Female subject, age 40–49. Located on the arm. This is a close-up image — 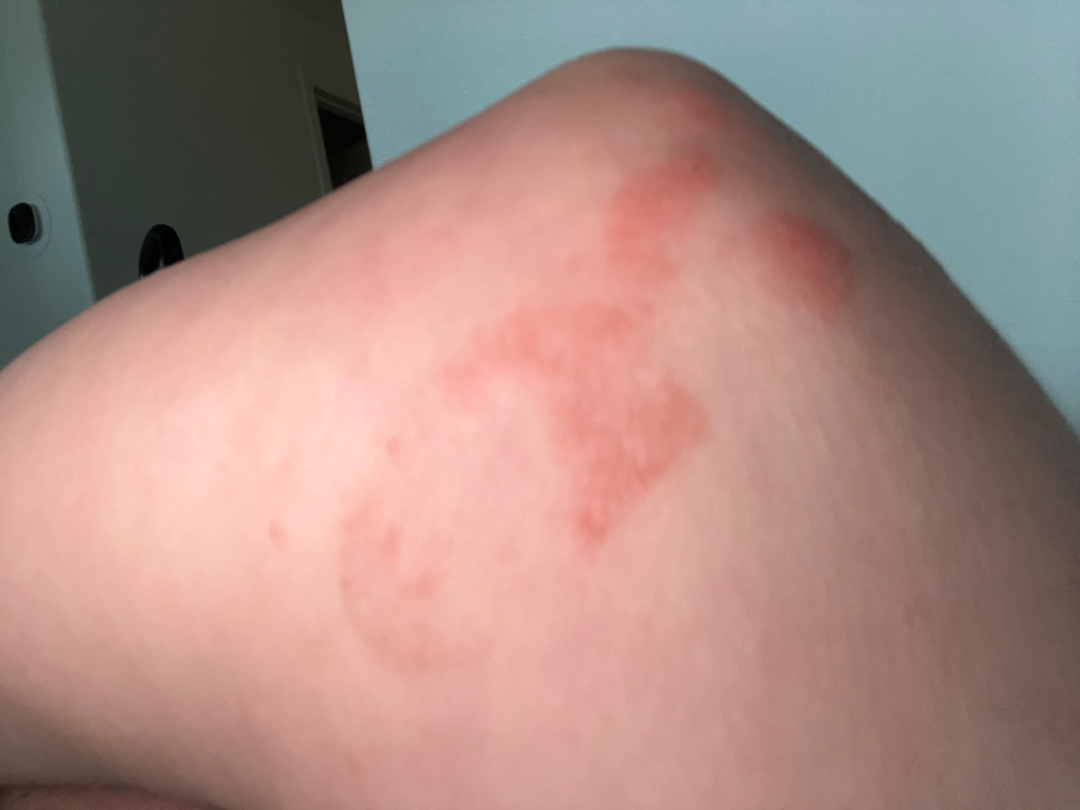Diagnostic features were not clearly distinguishable in this photograph.